The lesion involves the head or neck. This image was taken at an angle — 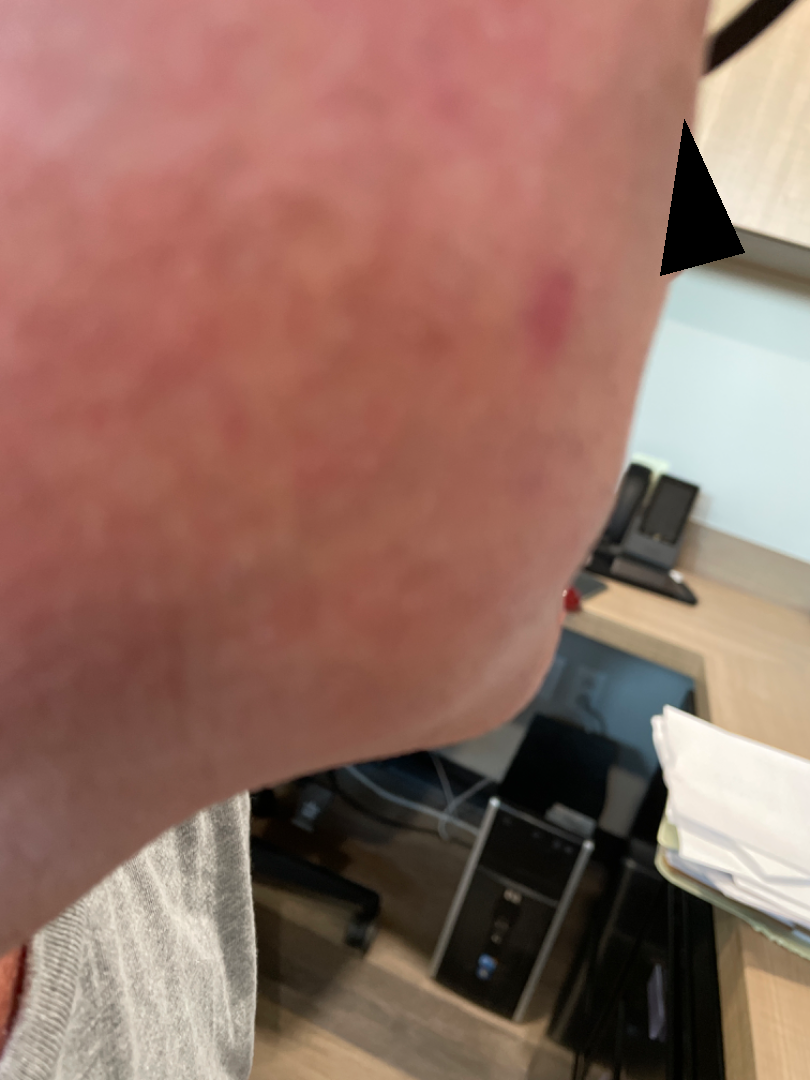Q: What was the assessment?
A: indeterminate from the photograph
Q: How does the lesion feel?
A: flat
Q: When did this start?
A: one to three months
Q: Reported symptoms?
A: itching